The contributor is a male aged 50–59. The affected area is the leg, palm, back of the hand and arm. The lesion is described as rough or flaky and flat. Reported lesion symptoms include bothersome appearance, itching and burning. This image was taken at an angle:
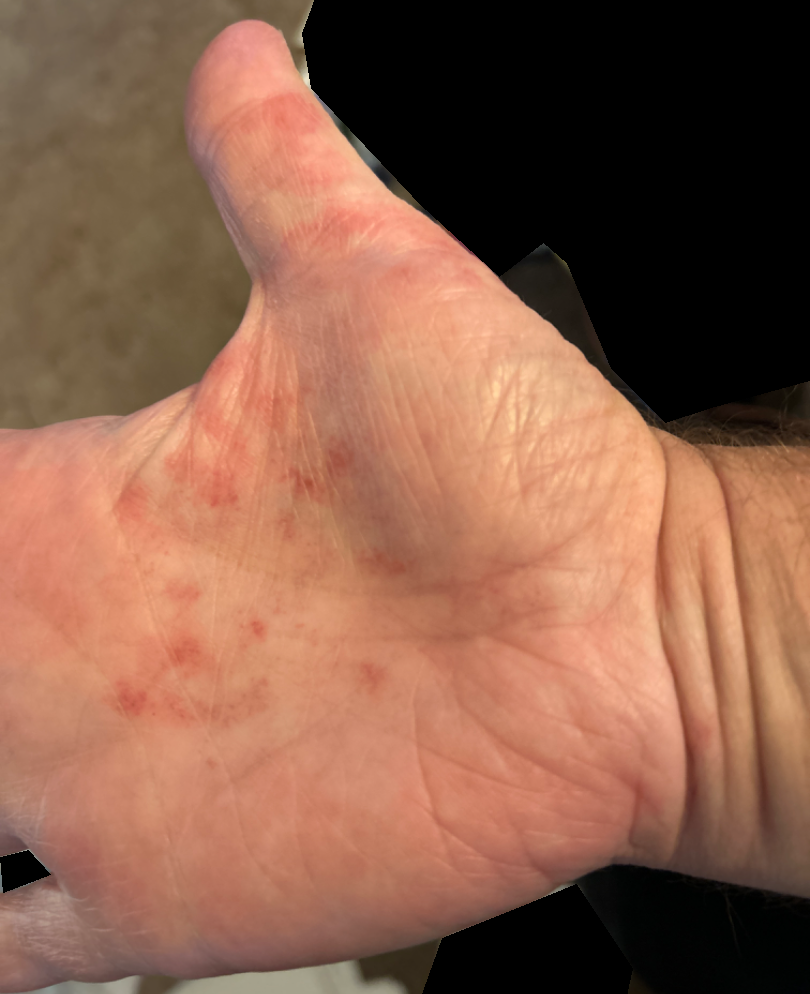  differential: Pigmented purpuric eruption